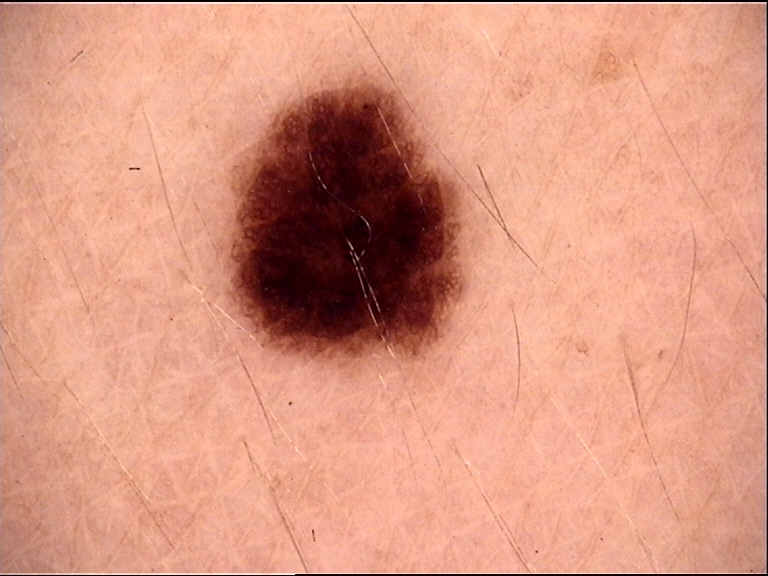Q: What was the diagnostic impression?
A: dysplastic junctional nevus (expert consensus)